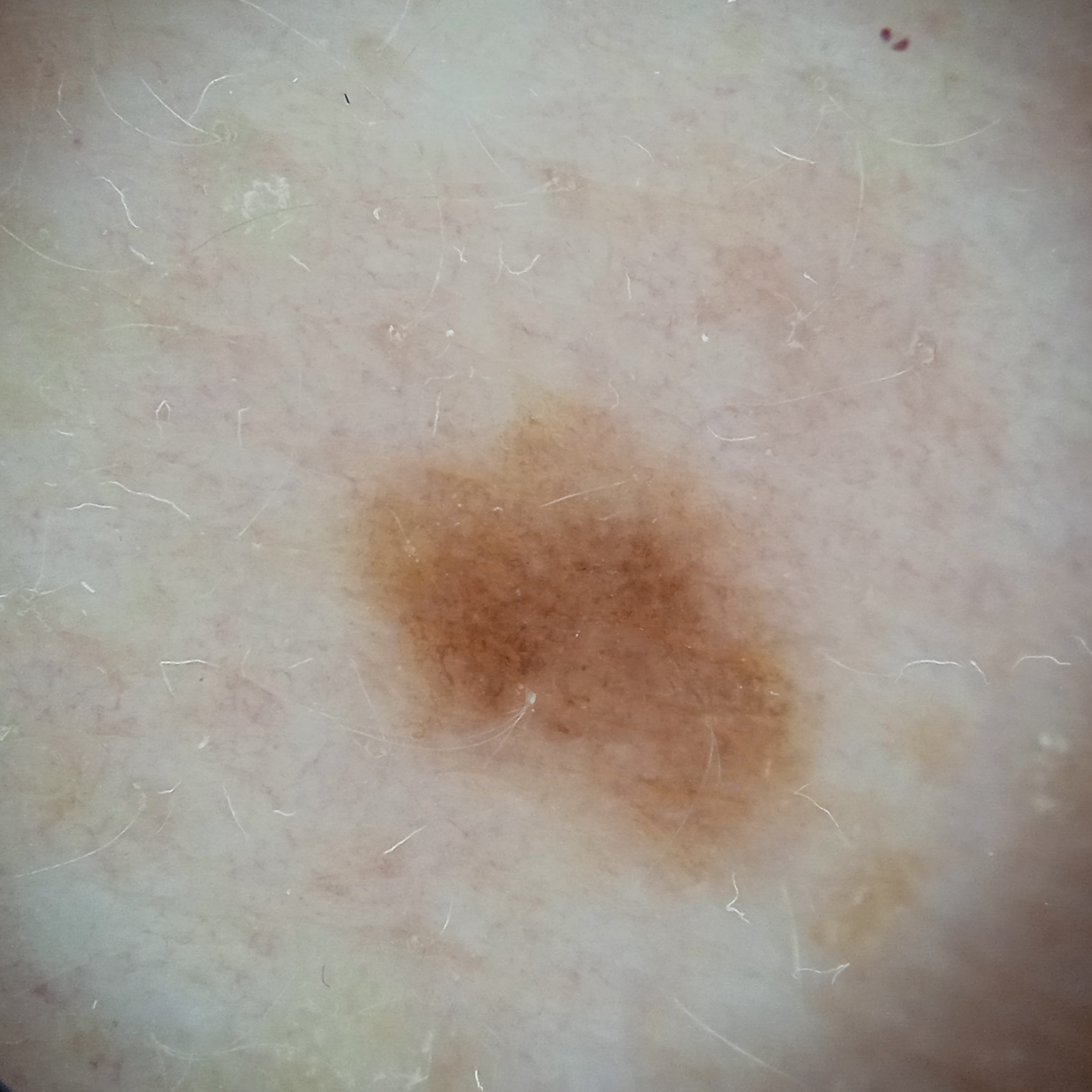<lesion>
<referral>research study (no referral diagnosis)</referral>
<image>dermoscopy</image>
<lesion_location>the back</lesion_location>
<lesion_size>
<diameter_mm>6.3</diameter_mm>
</lesion_size>
<diagnosis>
<name>melanocytic nevus</name>
<malignancy>benign</malignancy>
<certainty>good</certainty>
</diagnosis>
</lesion>